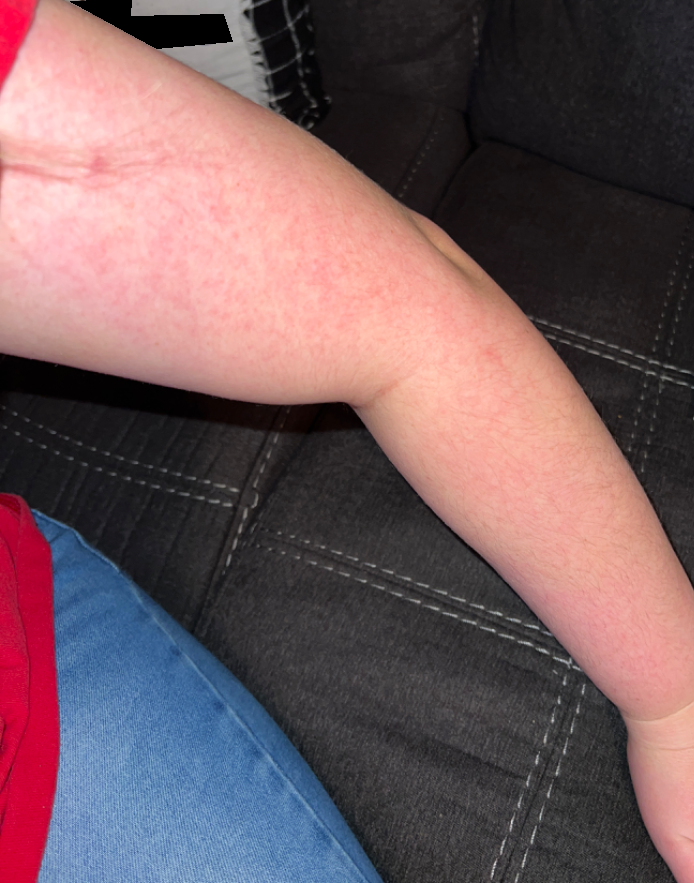The case was indeterminate on photographic review. The lesion involves the arm and head or neck. The lesion is described as flat. The condition has been present for less than one week. Symptoms reported: enlargement. The patient described the issue as a rash. An image taken at a distance. Female subject, age 18–29.